The patient notes the lesion is flat · this image was taken at a distance · Fitzpatrick III · located on the leg: 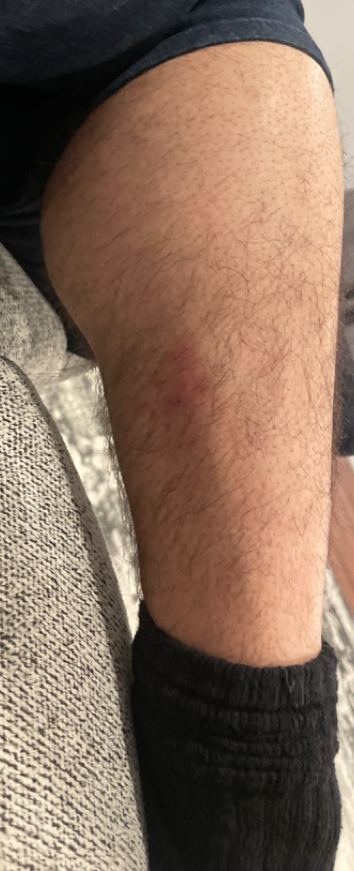Assessment:
The skin condition could not be confidently assessed from this image.